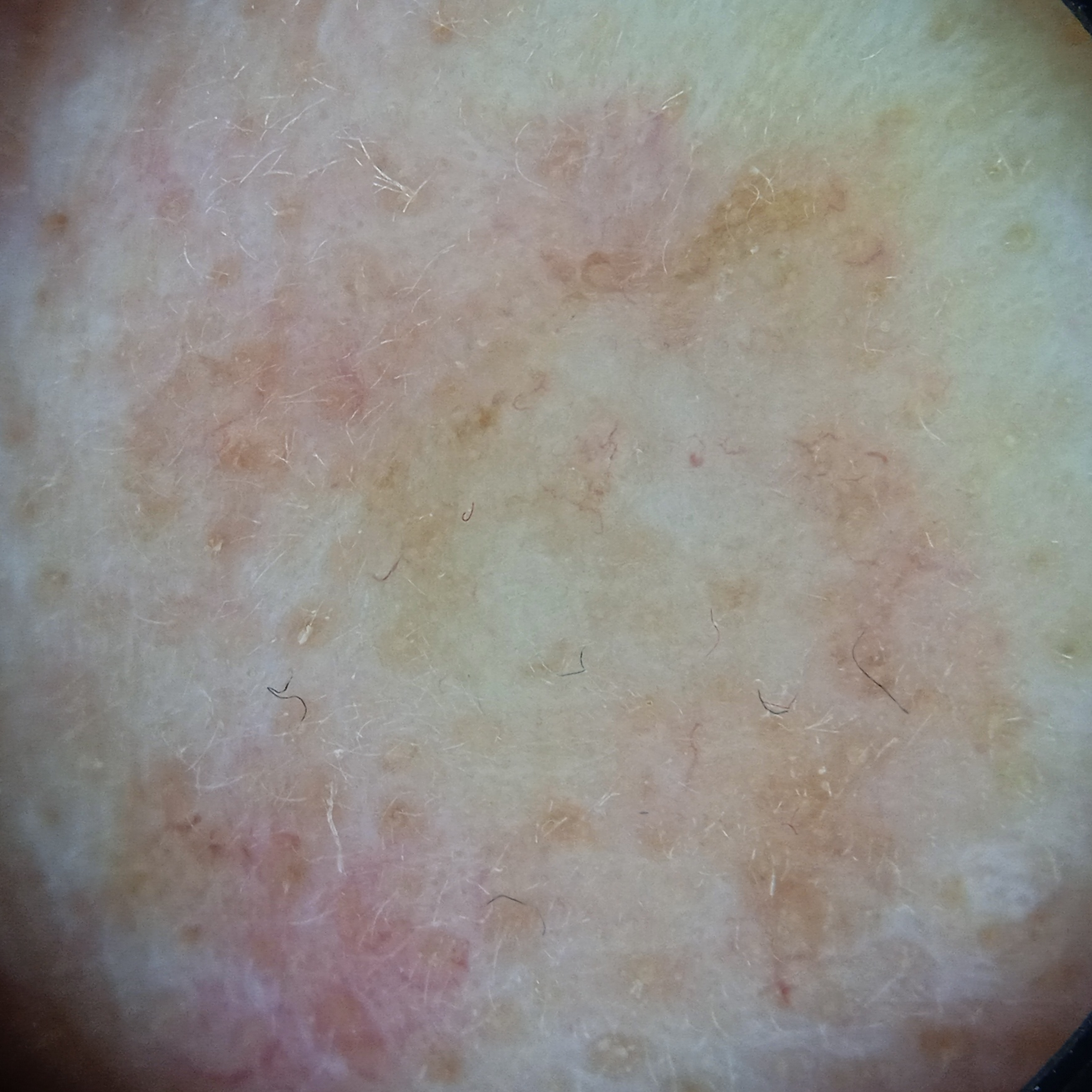By self-report, a personal history of cancer and no immunosuppression. A skin lesion imaged with a dermatoscope. A female subject age 84. The patient says their skin tans without first burning. Referred with a clinical suspicion of basal cell carcinoma. Few moles overall by the patient's own estimate. The lesion is located on the face. Histopathology confirmed a basal cell carcinoma, following excision, with a measured tumor thickness of 1.5 mm.